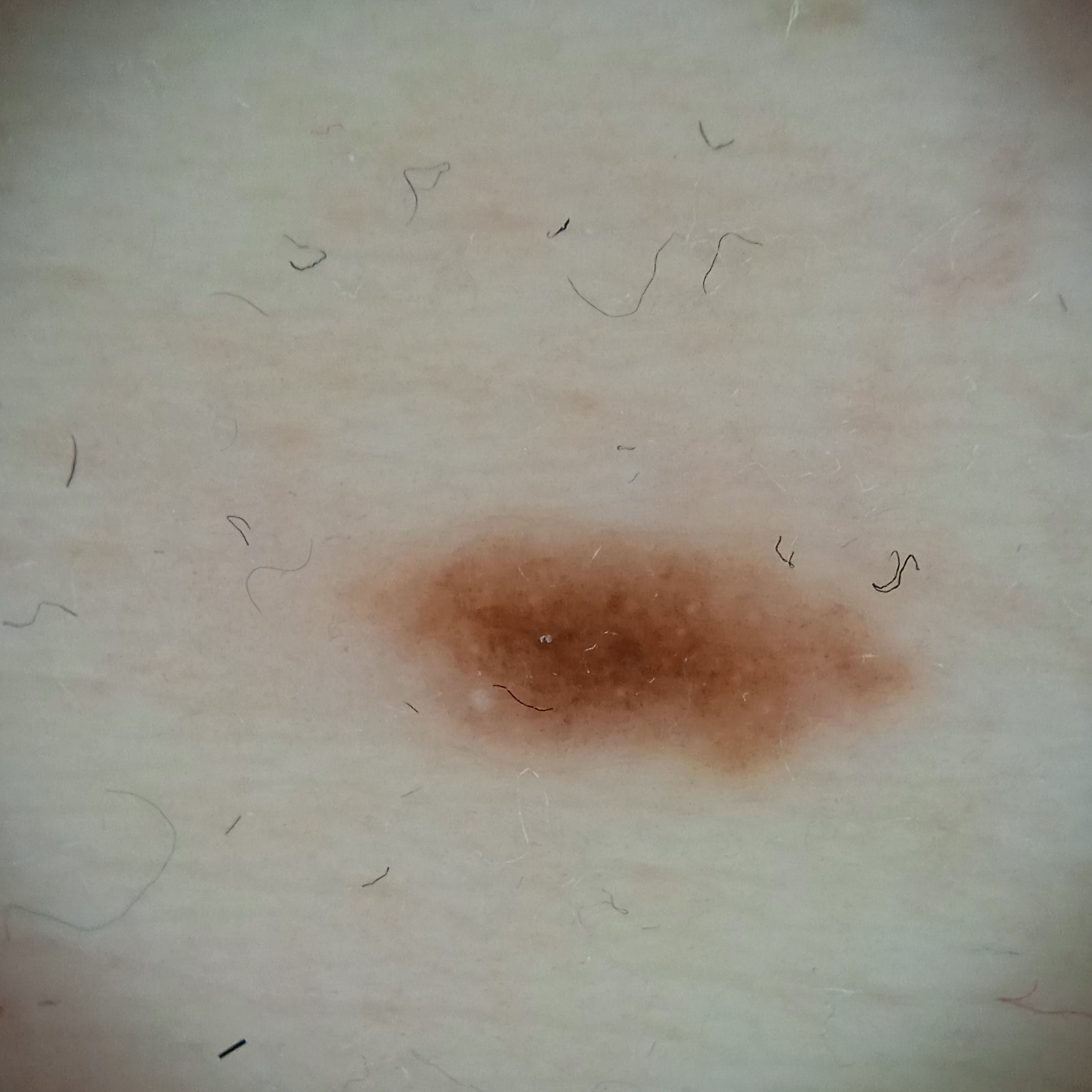Dermatologist review favored a melanocytic nevus.